A dermoscopy image of a single skin lesion. The patient is a male aged 68 to 72:
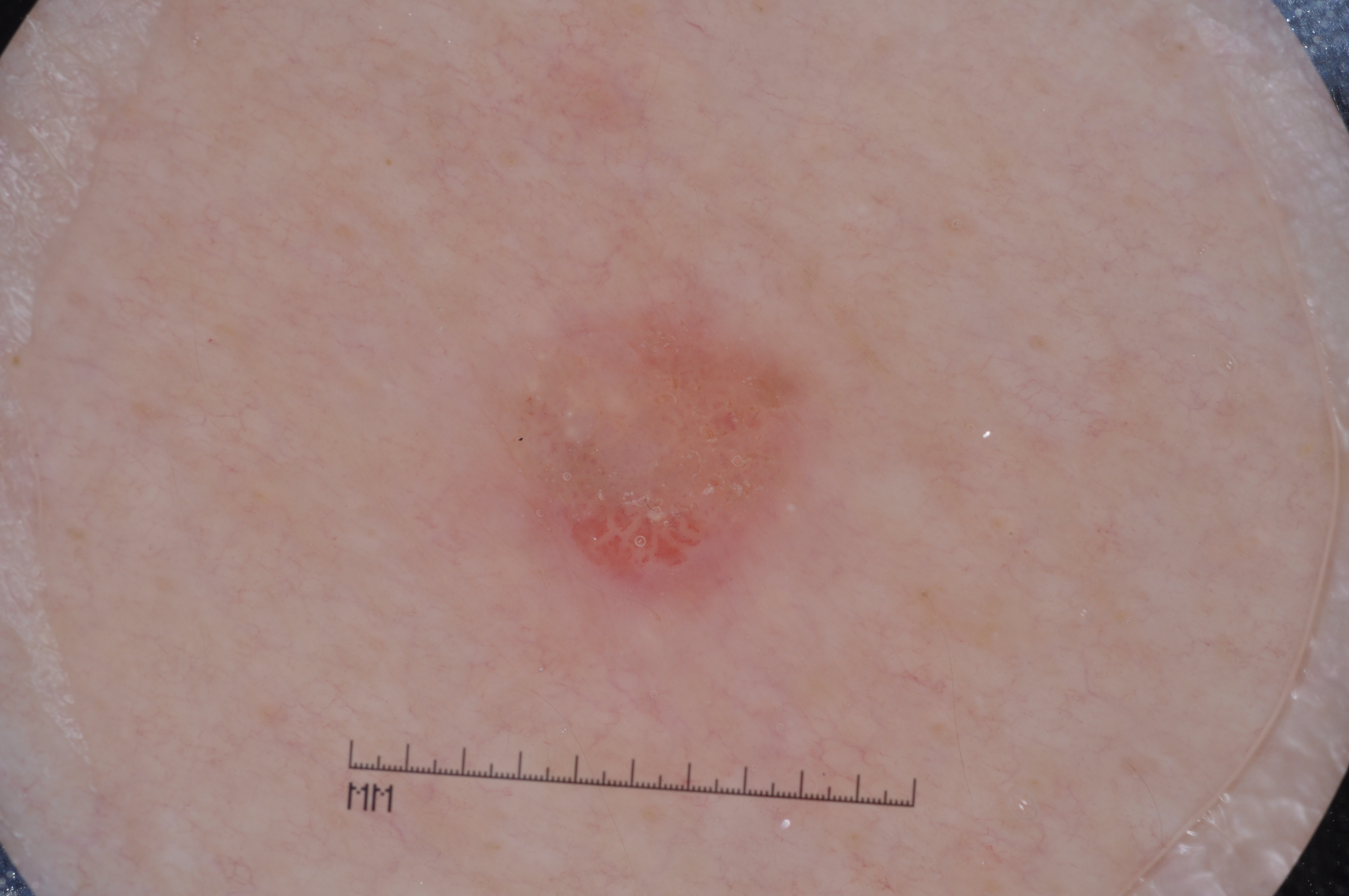Dermoscopic review identifies milia-like cysts. The lesion's extent is x1=485 y1=294 x2=822 y2=609. The lesion occupies roughly 6% of the field. Diagnosed as a seborrheic keratosis, a benign lesion.